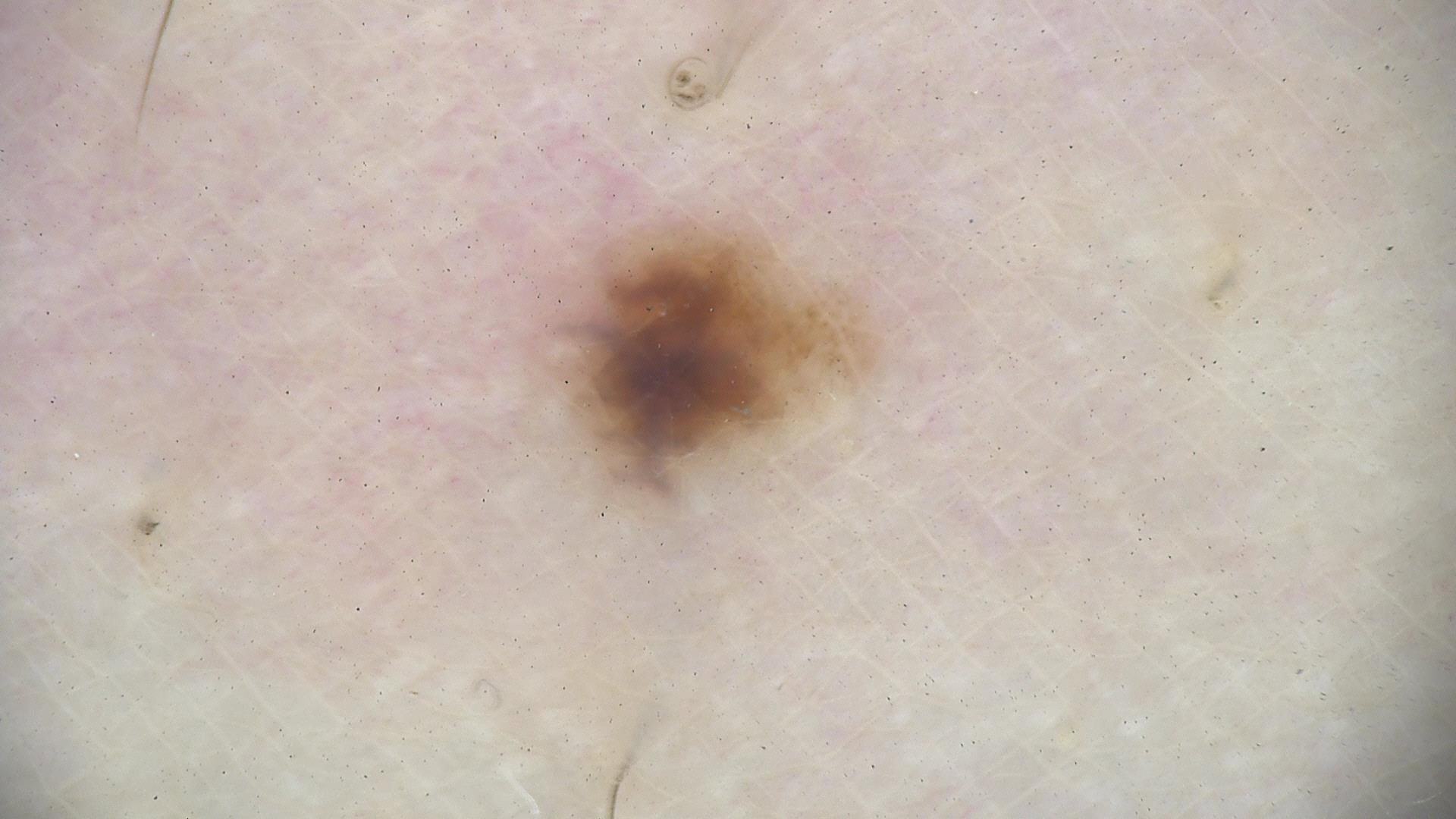Impression:
Classified as a dysplastic junctional nevus.